Collected as part of a research study, without a referral diagnosis; a male patient age 79; few moles overall by the patient's own estimate; by self-report, no immunosuppression; the patient says their skin tans without first burning; a skin lesion imaged with a dermatoscope: 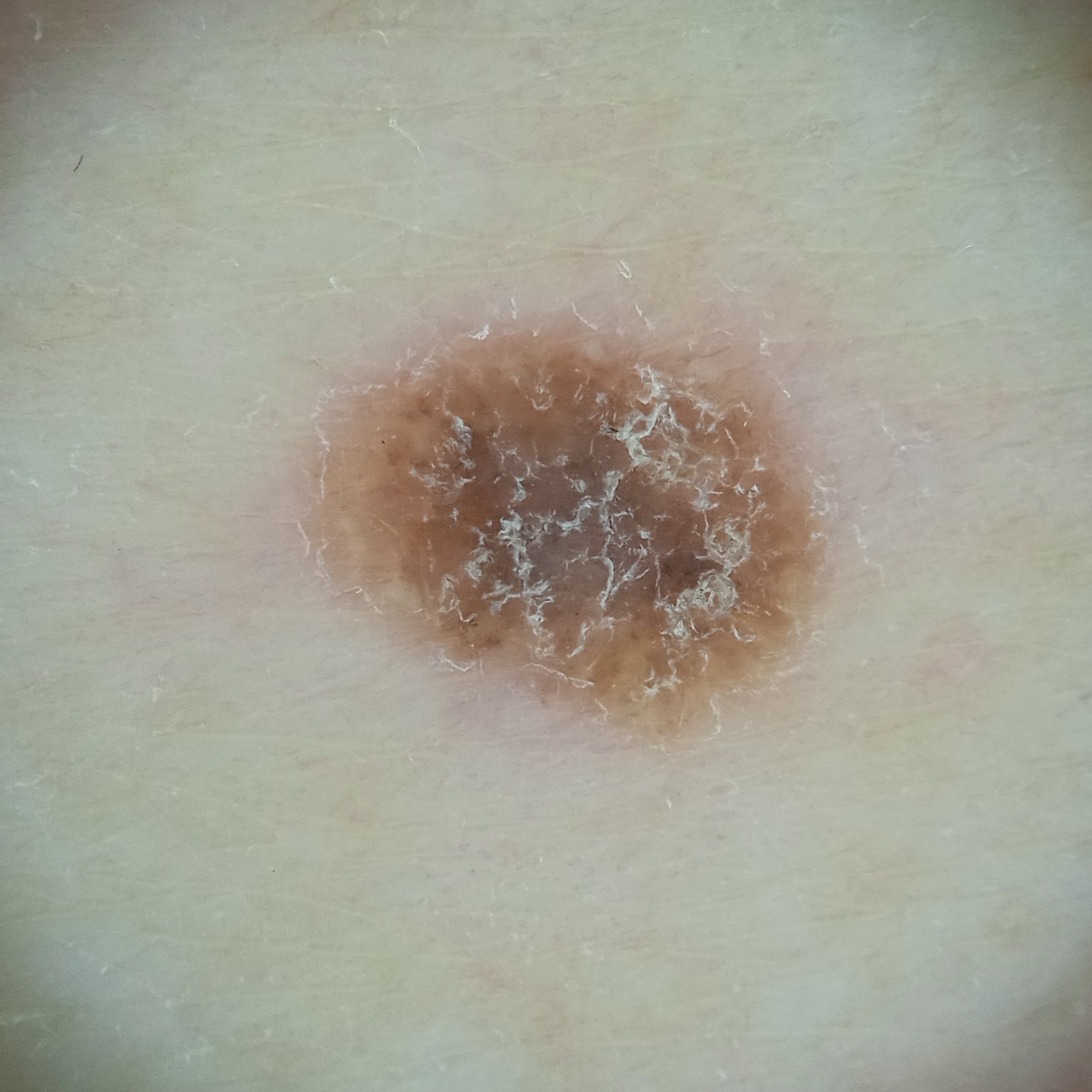Summary: The lesion measures approximately 5.9 mm. Impression: The dermatologists' assessment was a seborrheic keratosis.